Dermoscopy of a skin lesion:
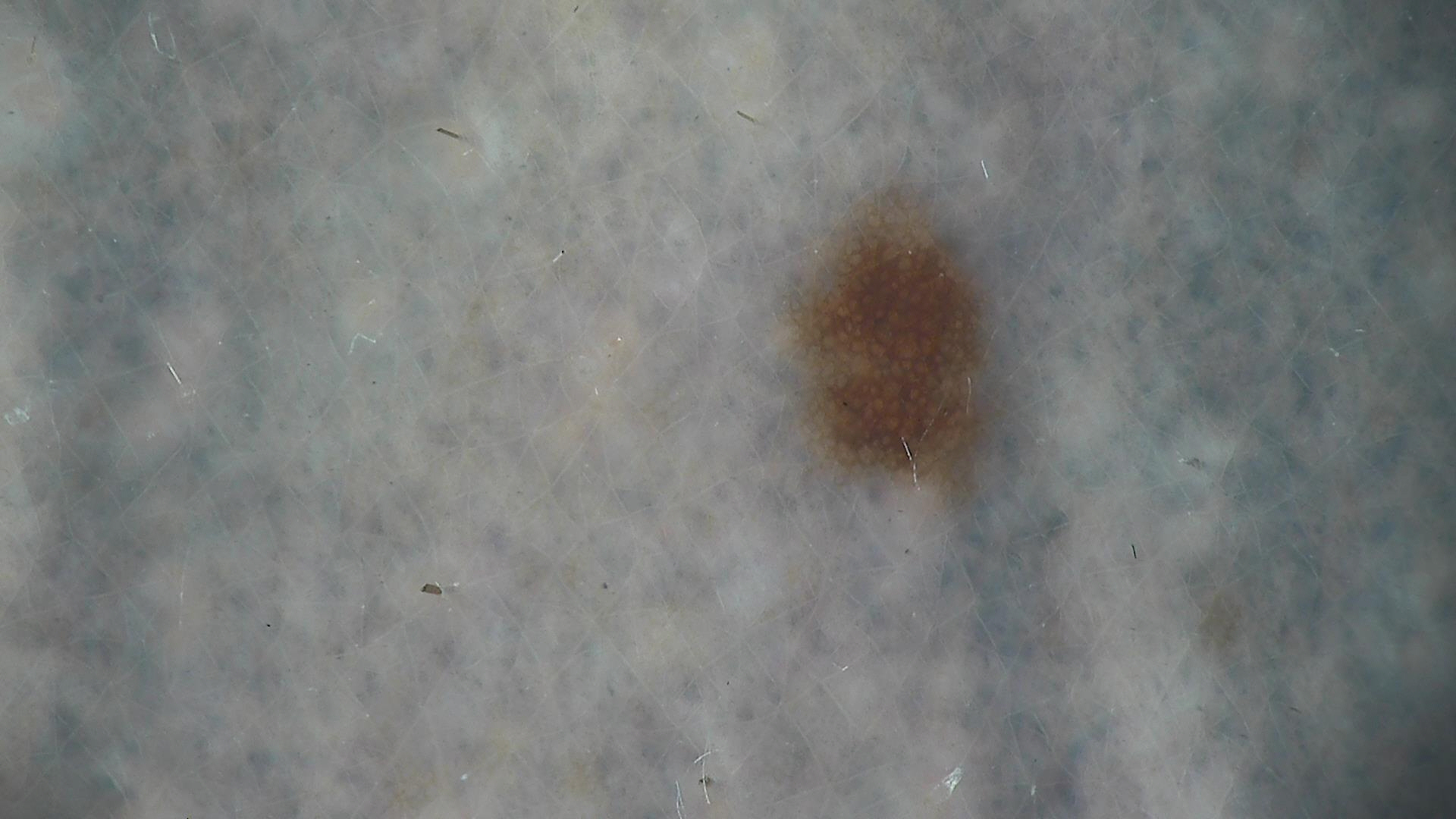  diagnosis:
    name: dysplastic junctional nevus
    code: jd
    malignancy: benign
    super_class: melanocytic
    confirmation: expert consensus